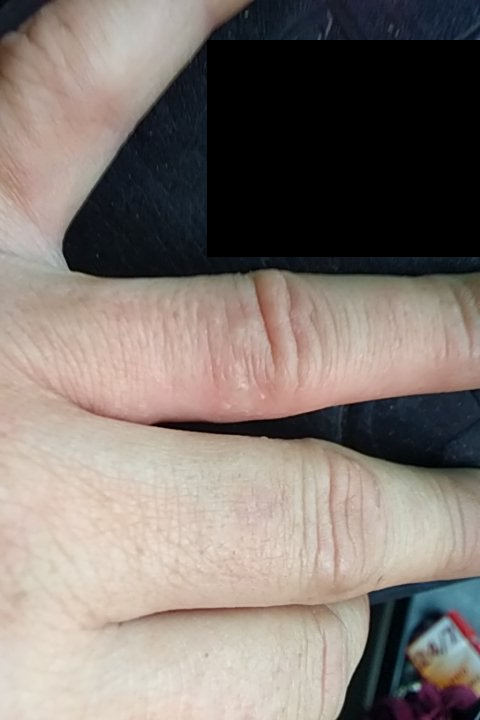assessment: could not be assessed
shot_type: at an angle